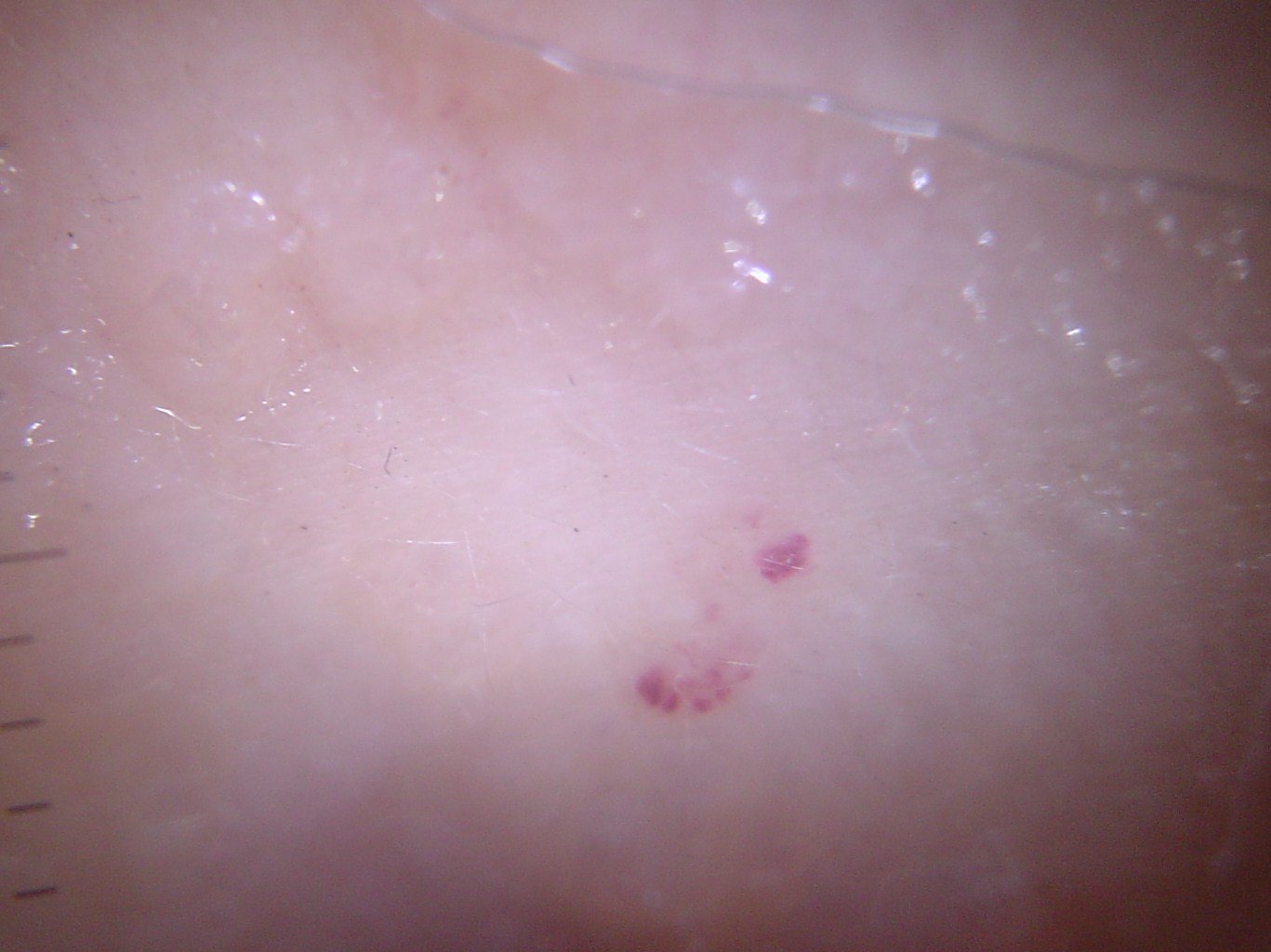A dermoscopic close-up of a skin lesion.
The diagnostic label was a benign lesion — a hemangioma.